The lesion is described as raised or bumpy and flat; symptoms reported: itching; this image was taken at a distance; located on the arm: 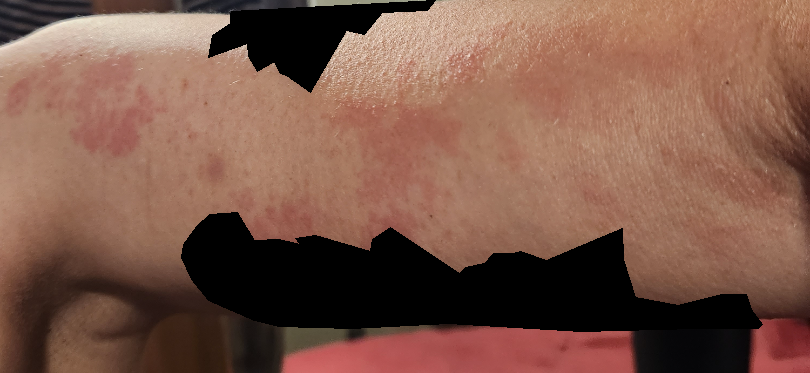The image was not sufficient for the reviewer to characterize the skin condition.